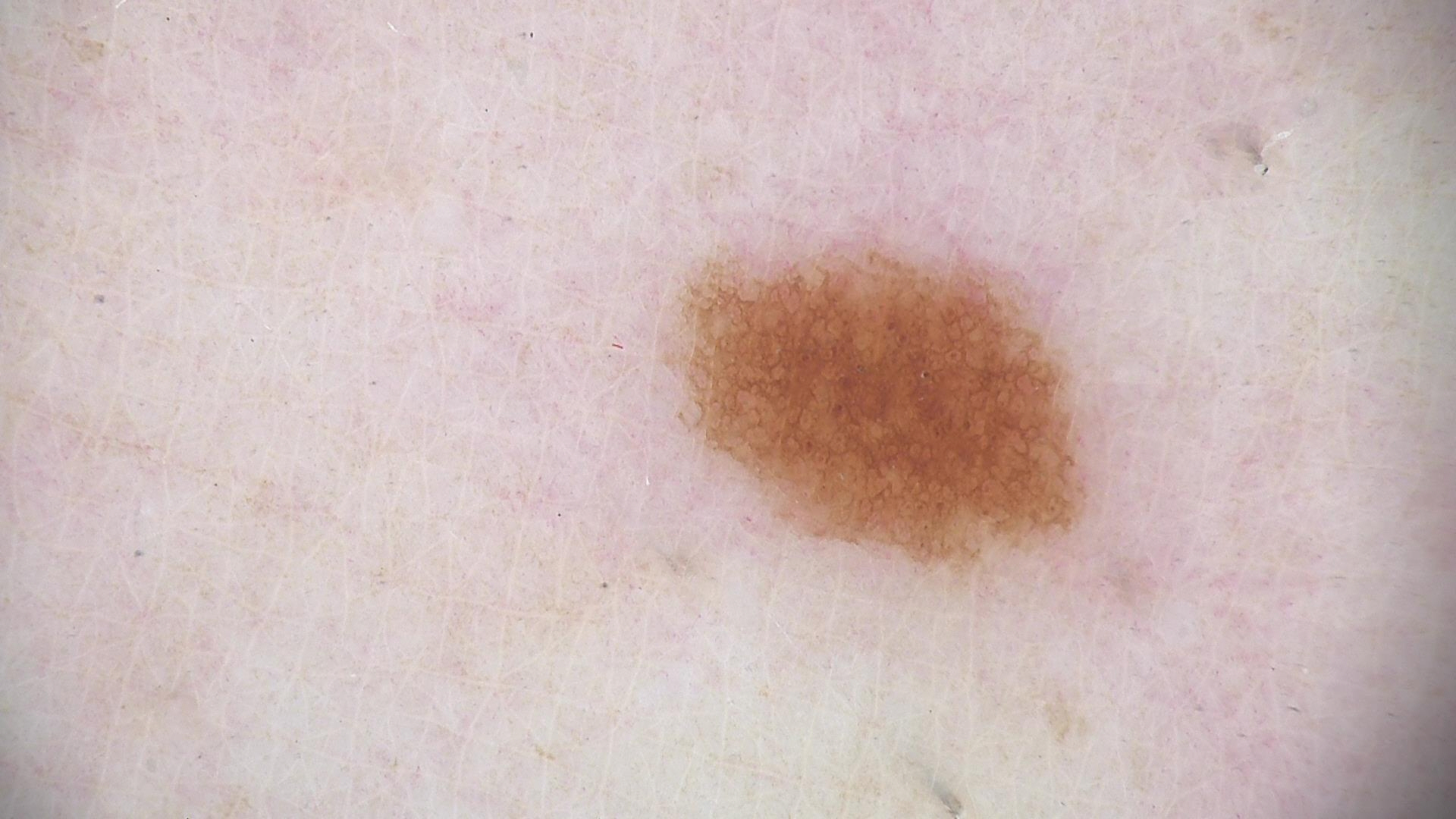modality — dermoscopy; lesion type — banal; diagnostic label — junctional nevus (expert consensus).